A clinical photo of a skin lesion taken with a smartphone.
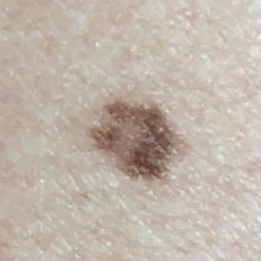Findings: Located on the back. The patient describes that the lesion has not bled and has not grown. Conclusion: Clinically diagnosed as a nevus.